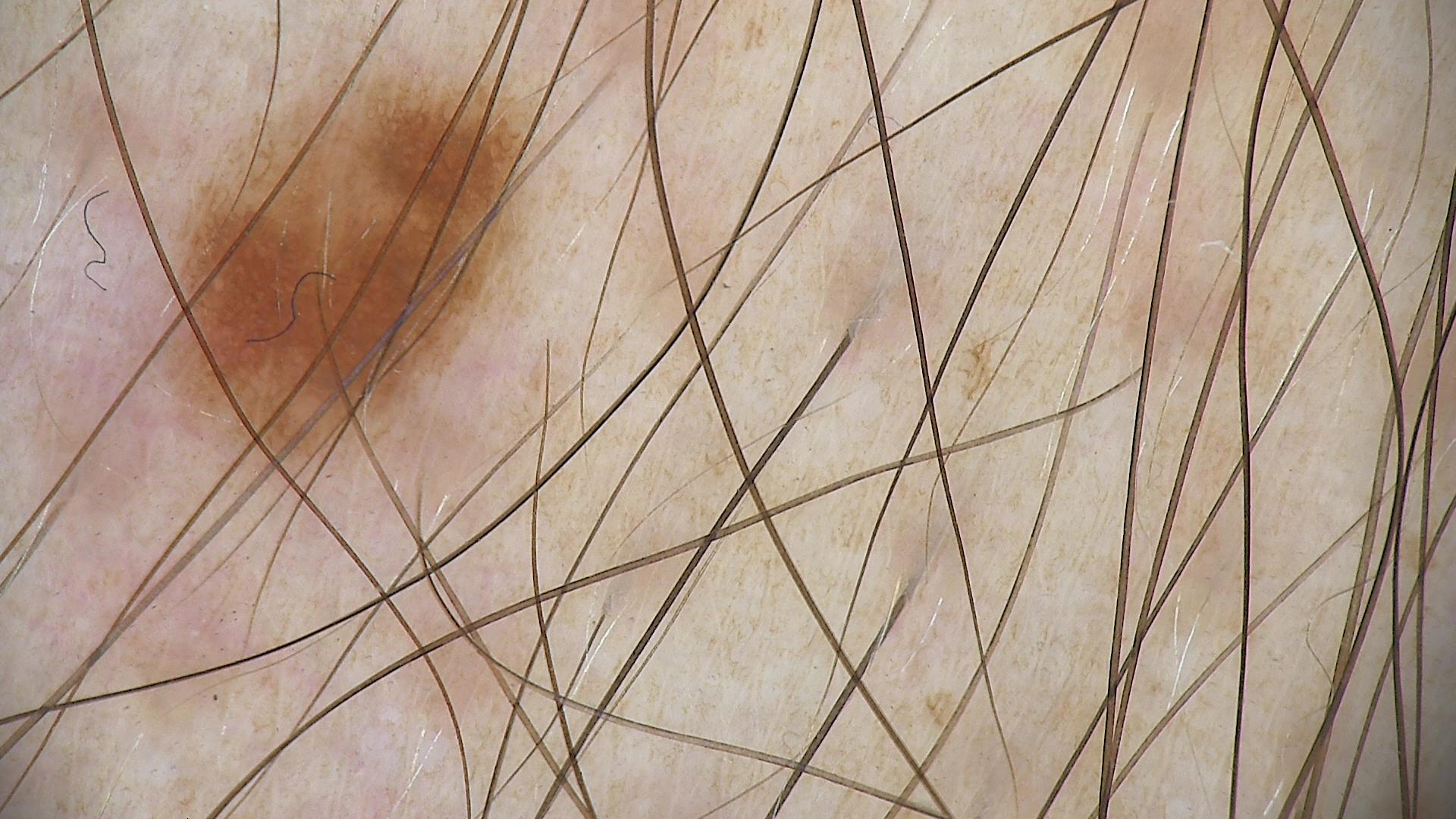imaging — dermatoscopy | class — dysplastic junctional nevus (expert consensus).